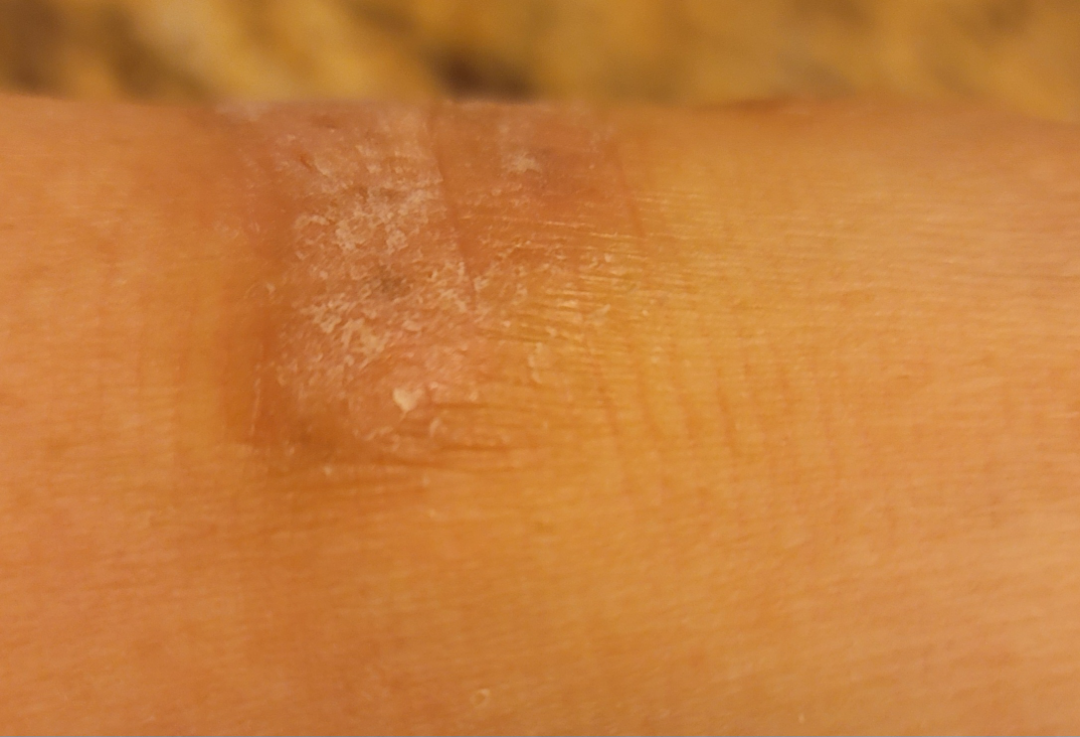* self-categorized as — a rash
* image framing — at an angle
* lesion symptoms — bothersome appearance and itching
* location — top or side of the foot
* patient — male
* history — more than five years
* diagnostic considerations — three independent reviewers: most consistent with Lichen Simplex Chronicus; also on the differential is Eczema; less probable is Psoriasis; less likely is Pemphigus vulgaris